The lesion involves the back of the hand, leg and arm; the condition has been present for more than one year; the lesion is described as rough or flaky; this is a close-up image; the lesion is associated with bothersome appearance and bleeding; the patient is a female aged 40–49:
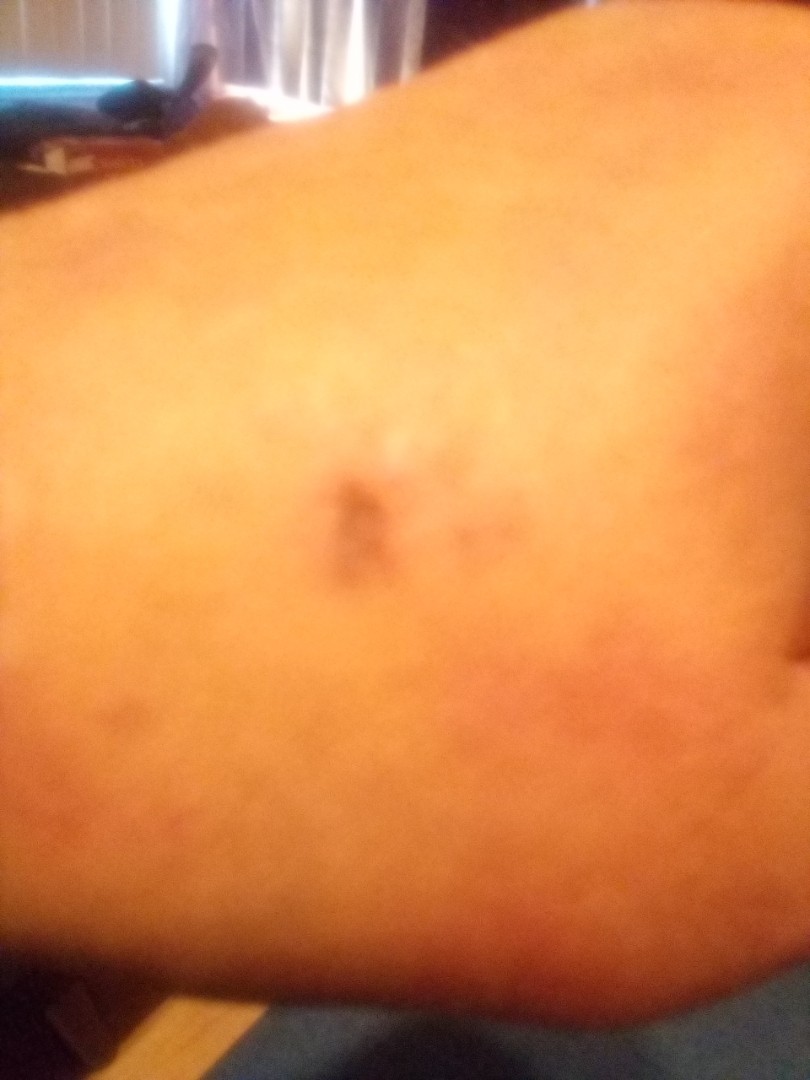The skin condition could not be confidently assessed from this image.